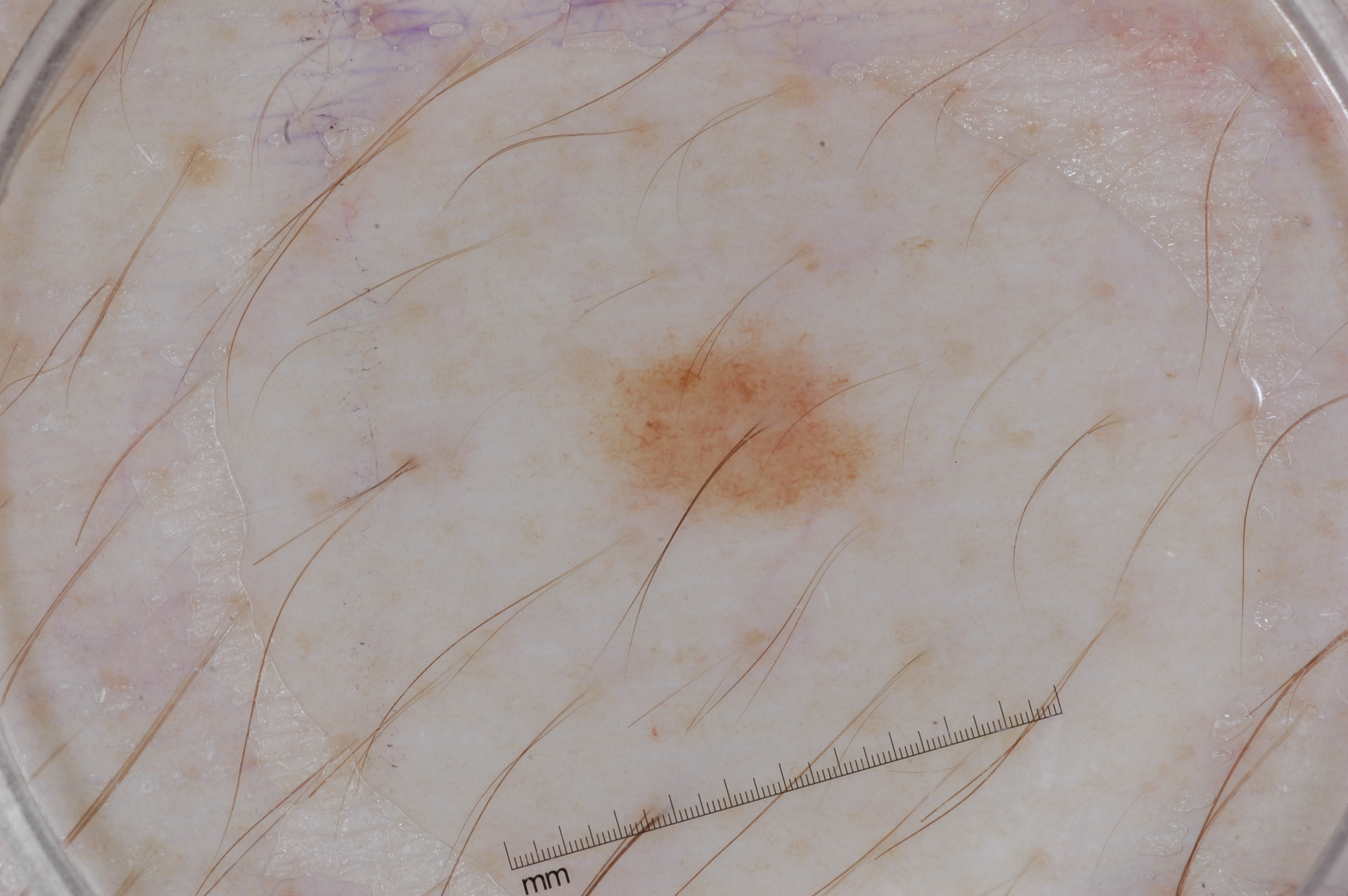A dermoscopy image of a single skin lesion. The lesion is small relative to the field of view. The lesion's extent is bbox(601, 322, 885, 518). Dermoscopic review identifies no streaks, negative network, pigment network, or milia-like cysts. The clinical diagnosis was a melanocytic nevus.